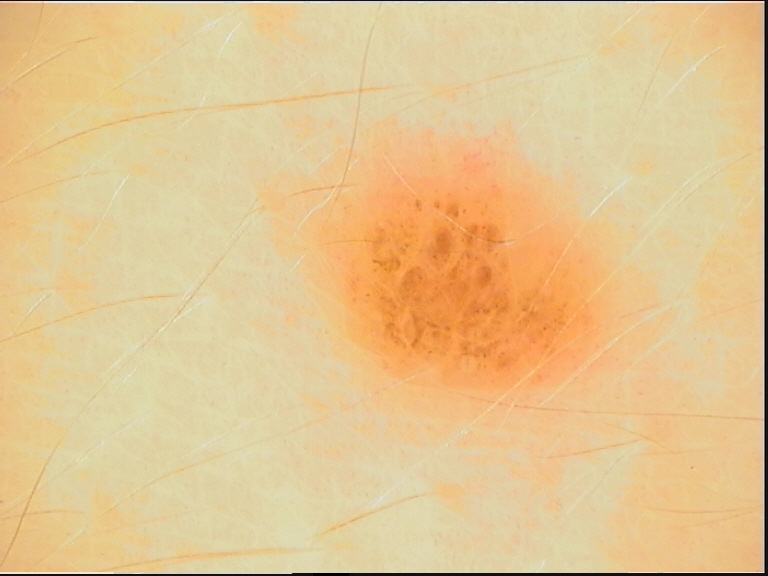– image type · dermatoscopy
– diagnosis · dysplastic compound nevus (expert consensus)